The patient is a female aged 58-62; this is a dermoscopic photograph of a skin lesion — 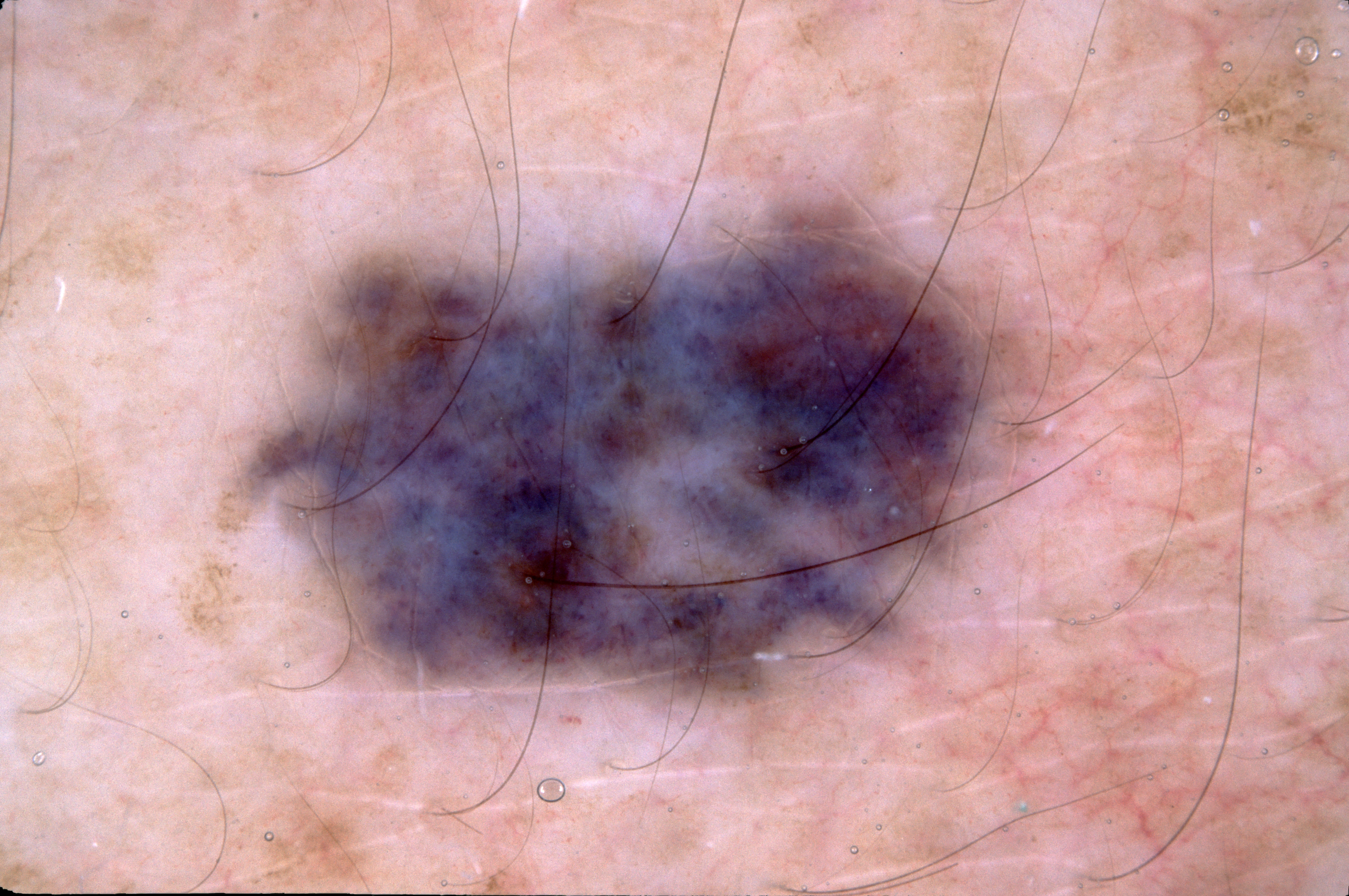absent dermoscopic features: negative network, streaks, pigment network, and milia-like cysts
bounding box: box(180, 157, 1097, 719)
size: large
diagnostic label: a melanocytic nevus, a benign lesion